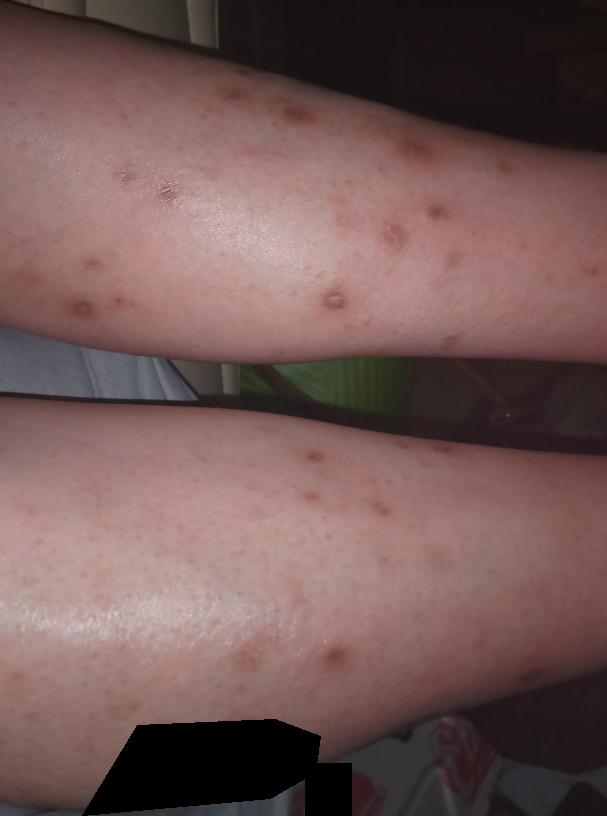{
  "shot_type": "at an angle",
  "duration": "more than one year",
  "patient": "female",
  "symptoms": "darkening",
  "body_site": [
    "arm",
    "leg"
  ],
  "texture": [
    "rough or flaky",
    "fluid-filled"
  ],
  "differential": {
    "leading": [
      "Prurigo nodularis"
    ],
    "considered": [
      "Folliculitis",
      "Insect Bite"
    ],
    "unlikely": [
      "Eczema",
      "Vasculitis of the skin"
    ]
  }
}